This is a close-up image; the lesion involves the arm:
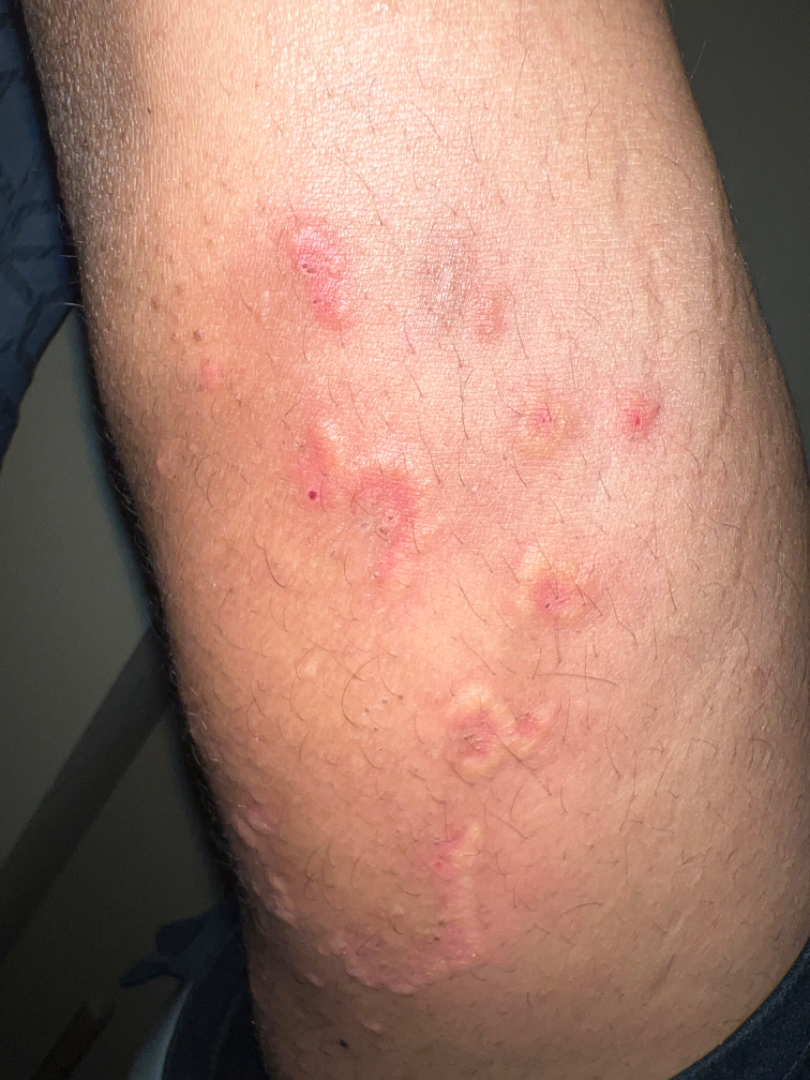* assessment · most consistent with Leukocytoclastic Vasculitis; the differential also includes Erythema annulare centrifugum